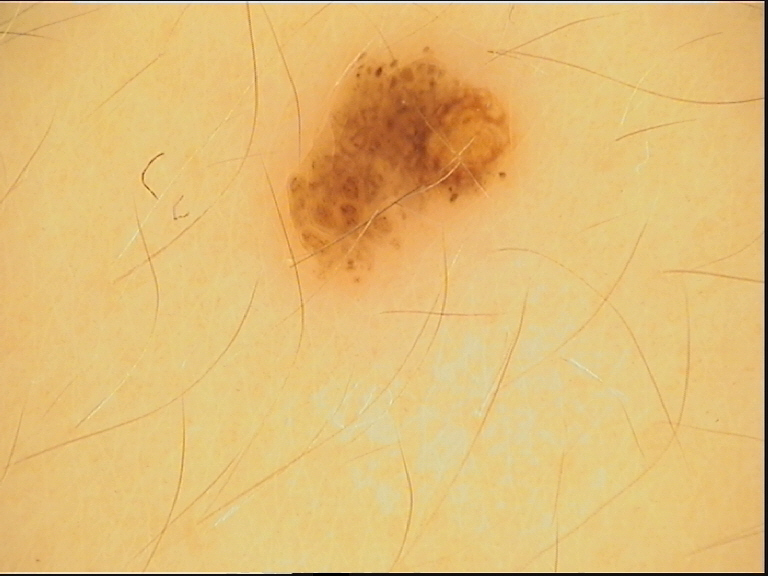Conclusion: The diagnosis was a dysplastic junctional nevus.